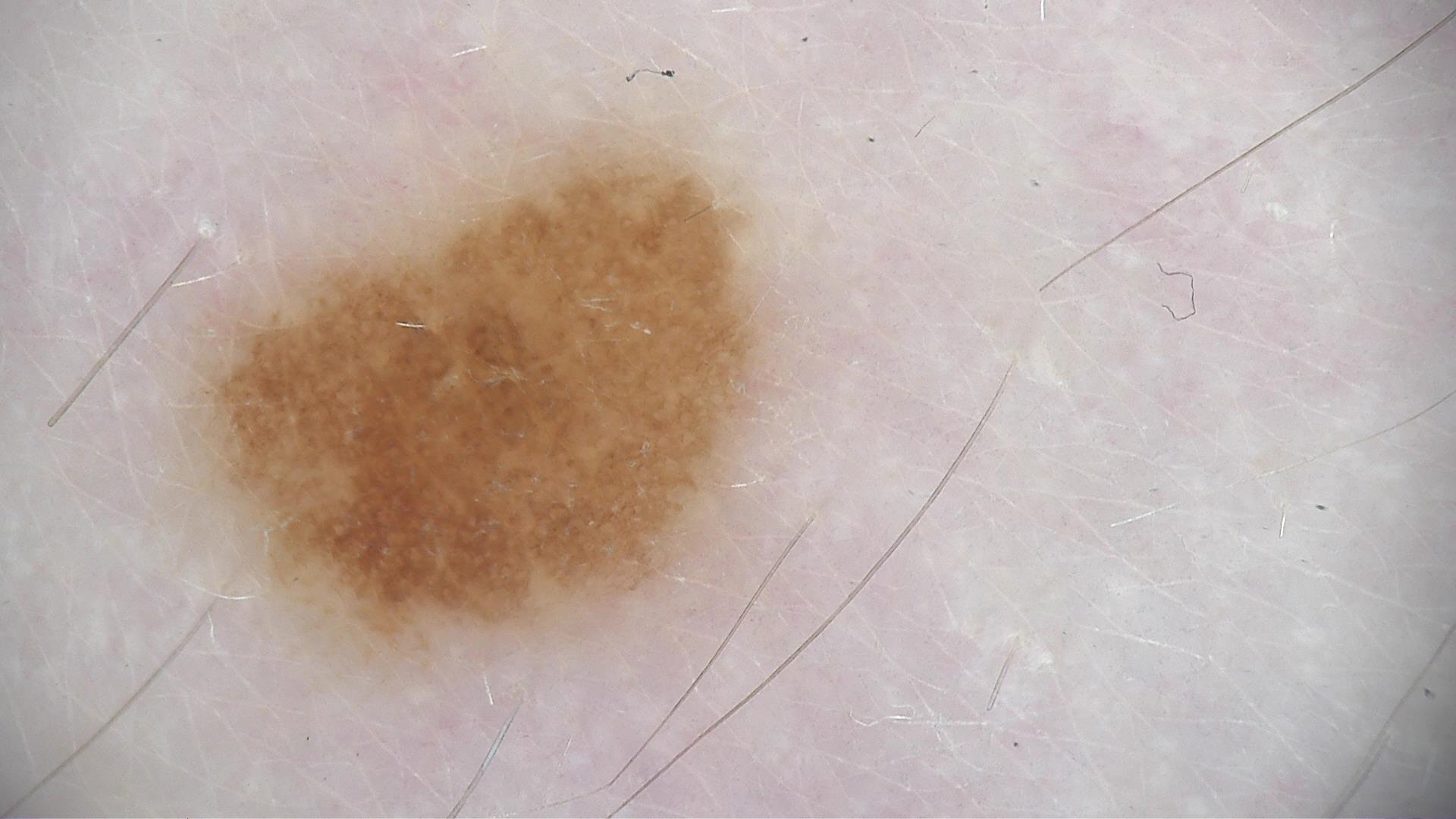modality: dermatoscopy; category: banal; diagnosis: compound nevus (expert consensus).